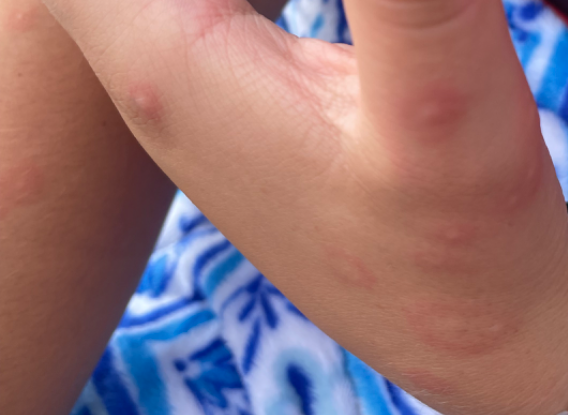History:
The photograph was taken at an angle. Located on the palm, leg and arm. The patient is a female aged 18–29.
Impression:
On teledermatology review: the leading consideration is Erythema multiforme; also raised was Drug Rash.